The subject is a male about 70 years old · dermoscopy of a skin lesion:
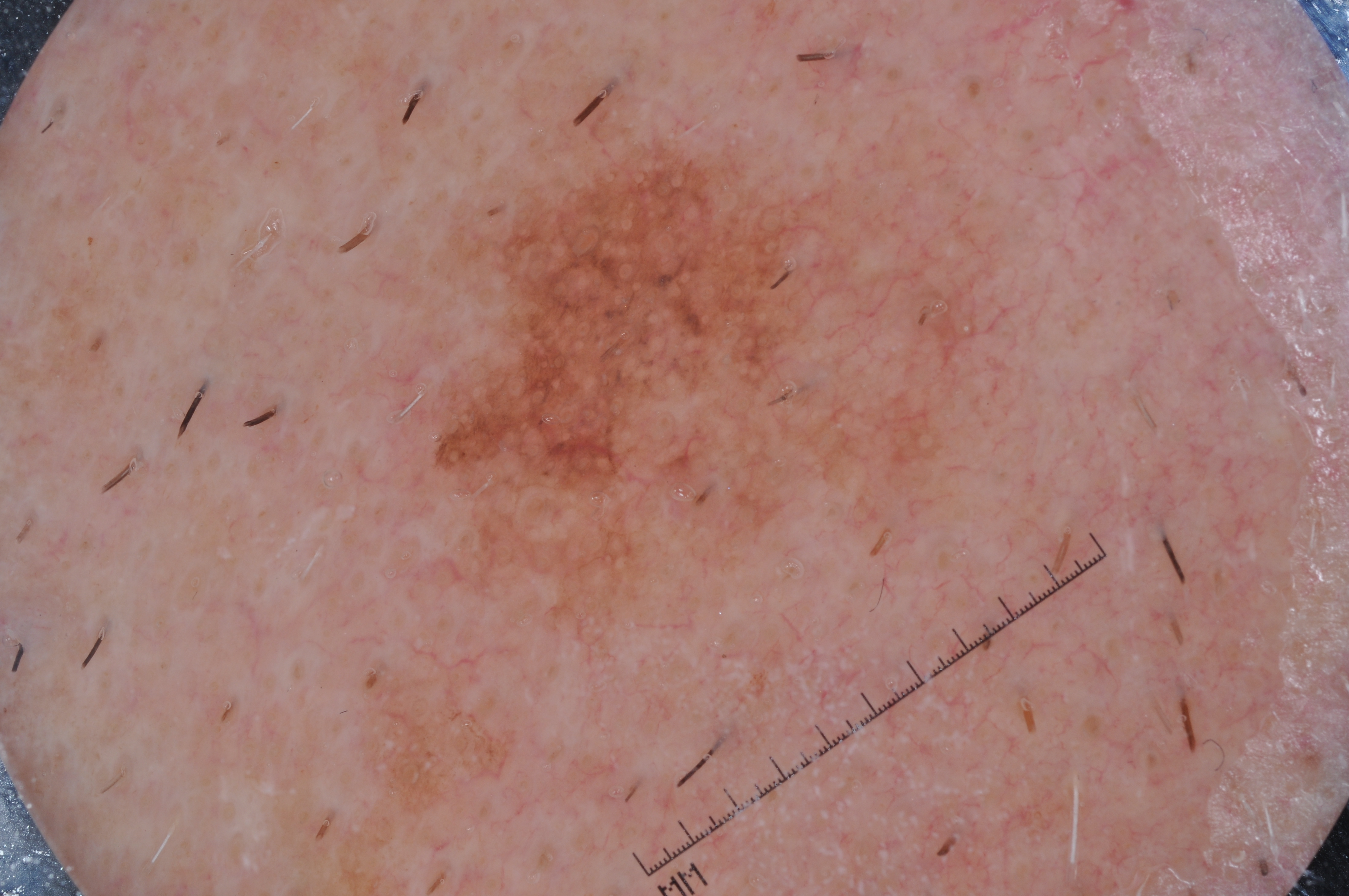Image and clinical context: Dermoscopic examination shows milia-like cysts. As (left, top, right, bottom), the lesion spans 277/101/1064/866. A prominent lesion filling much of the field. Conclusion: Confirmed on histopathology as a melanoma, a malignant lesion.